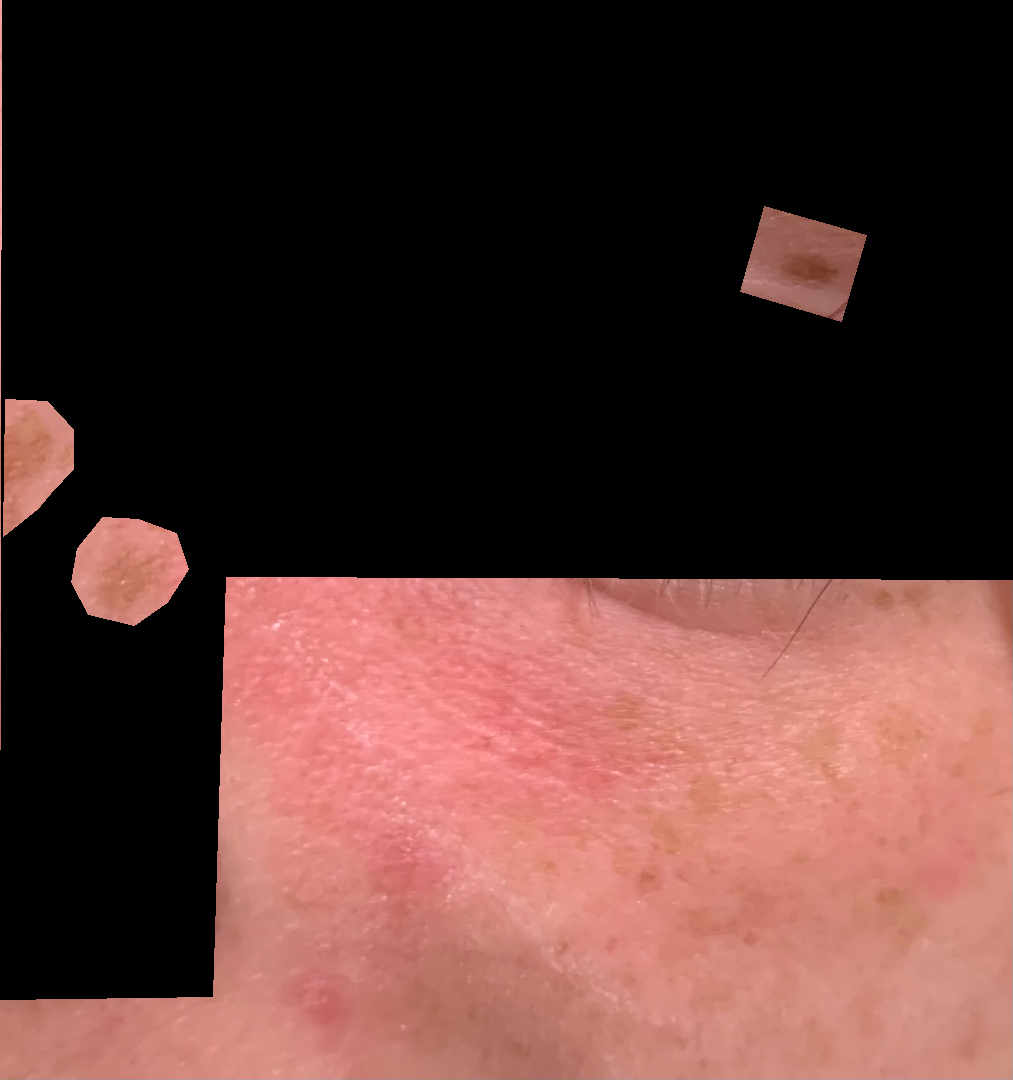The subject is a female aged 18–29.
This is a close-up image.
The affected area is the head or neck and leg.